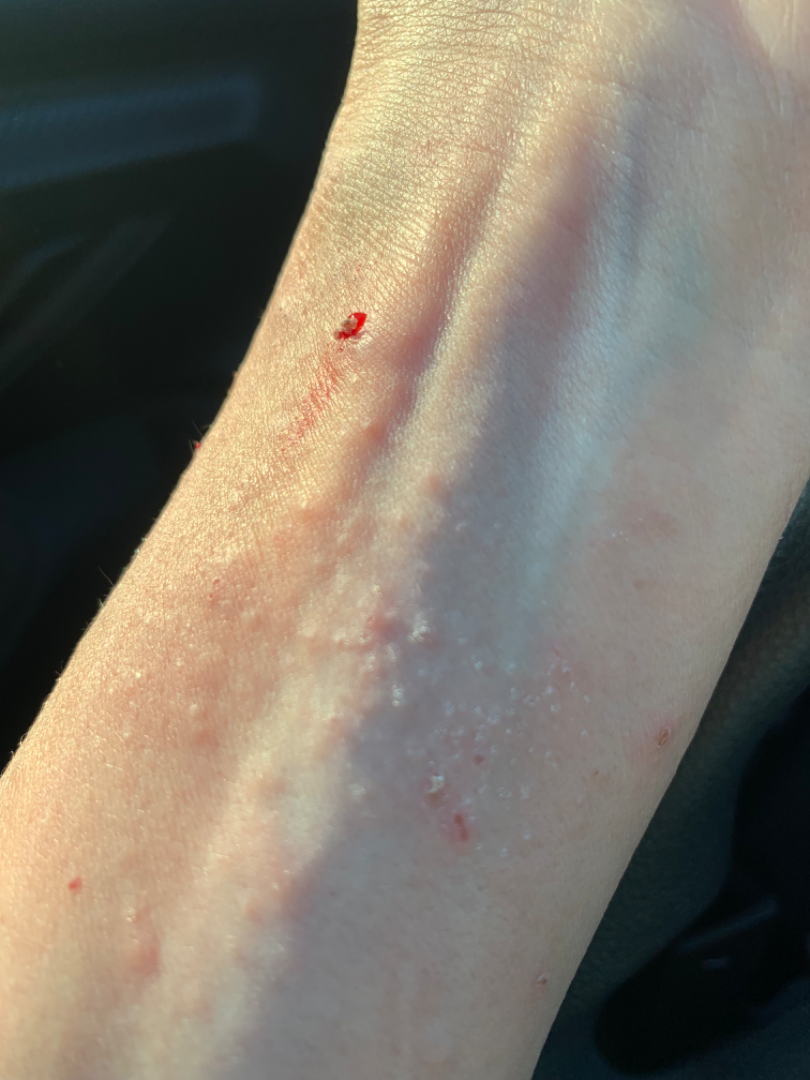Assessment:
On photographic review, the favored diagnosis is Allergic Contact Dermatitis; possibly Eczema; a more distant consideration is Urticaria.